This image was taken at an angle. The lesion involves the arm: 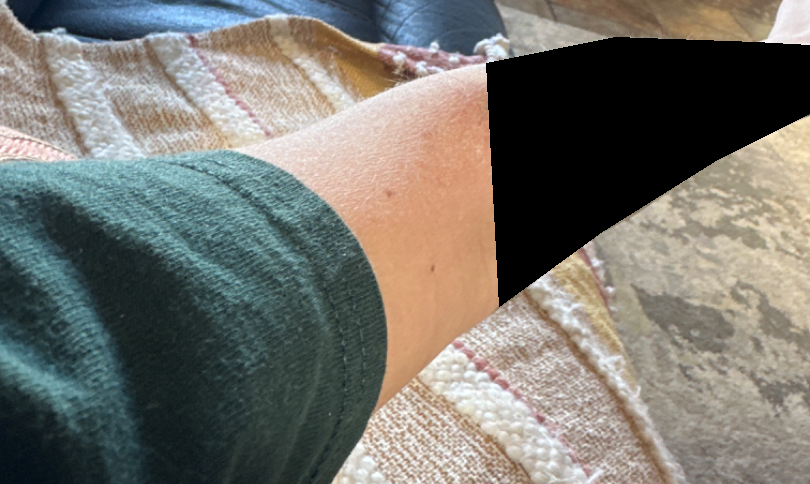Review:
On remote review of the image, Eczema (1.00).